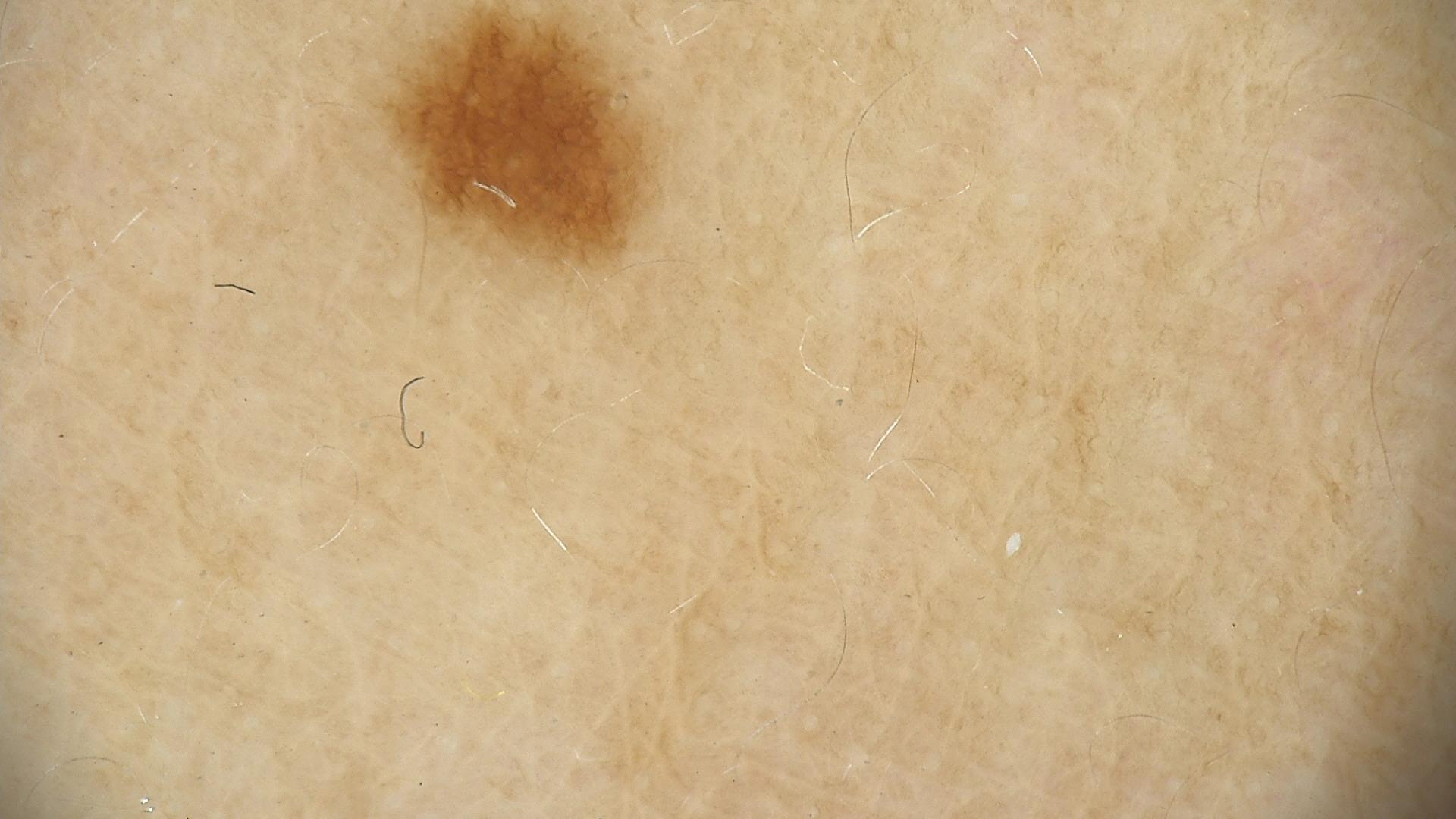Impression: The diagnosis was a dysplastic junctional nevus.